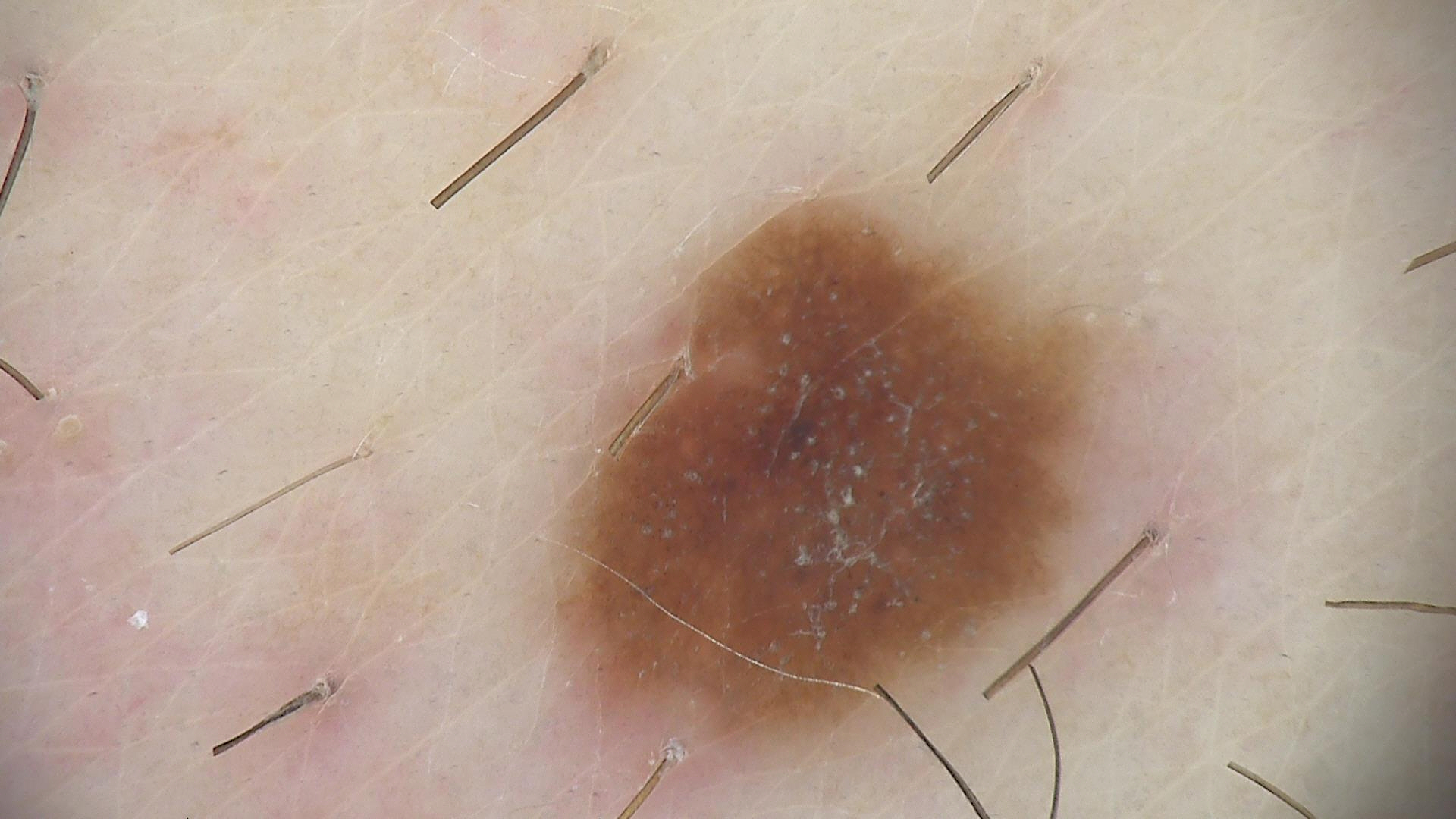{
  "image": "dermoscopy",
  "diagnosis": {
    "name": "dysplastic junctional nevus",
    "code": "jd",
    "malignancy": "benign",
    "super_class": "melanocytic",
    "confirmation": "expert consensus"
  }
}